A clinical photograph showing a skin lesion; a patient aged 9 — 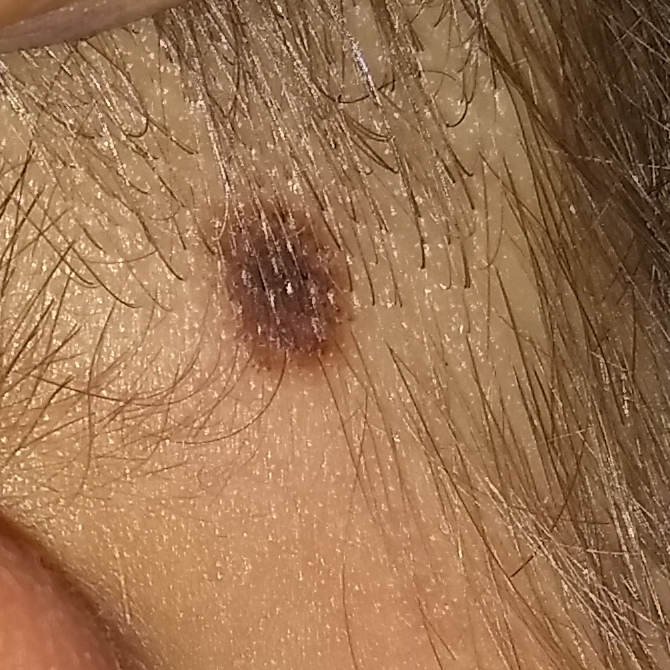Findings:
The lesion is located on the face. Asymptomatic by report.
Impression:
The consensus clinical diagnosis was a benign lesion — a nevus.